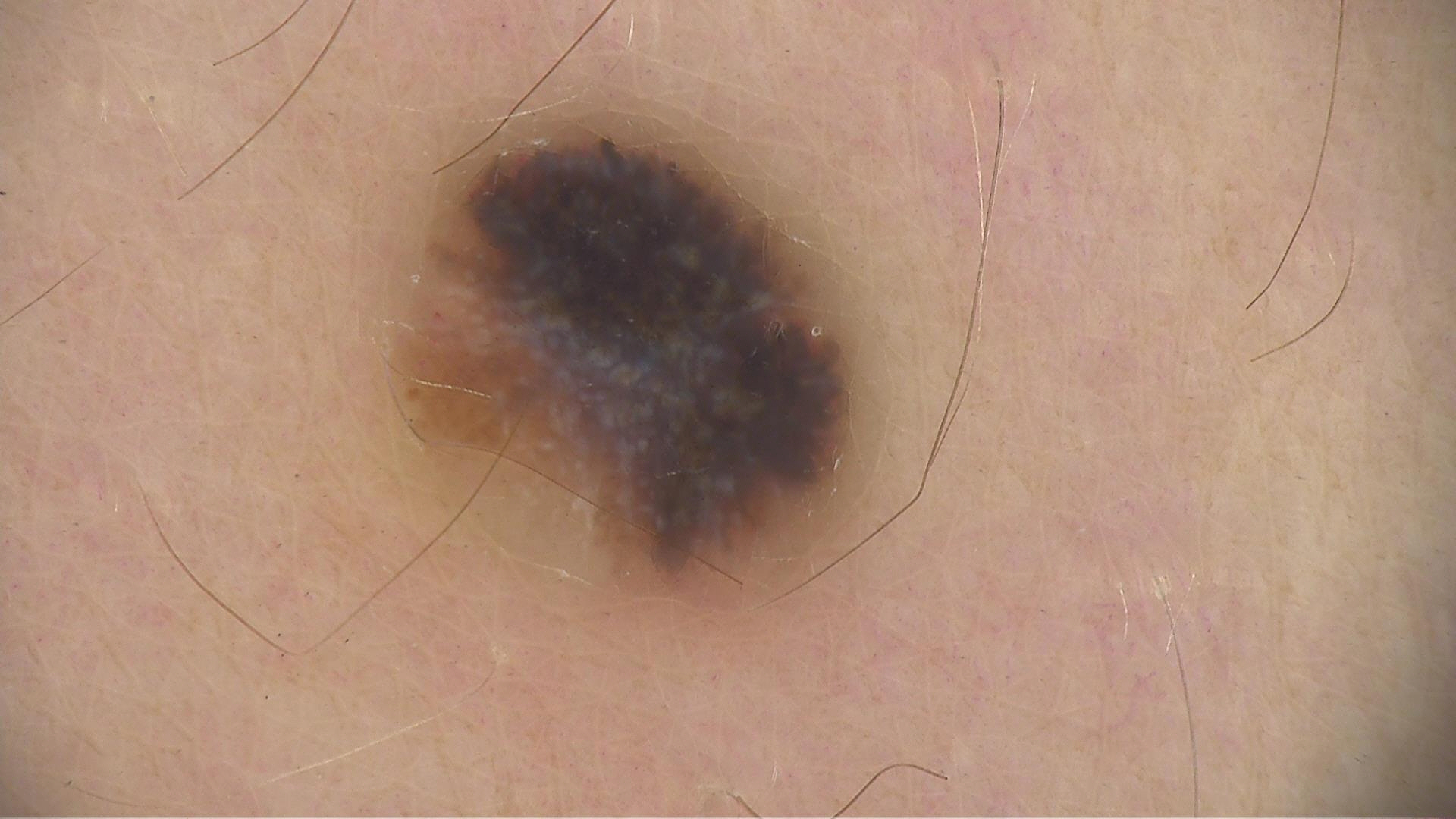A skin lesion imaged with a dermatoscope.
Histopathology confirmed a melanoma.